Dermoscopy of a skin lesion:
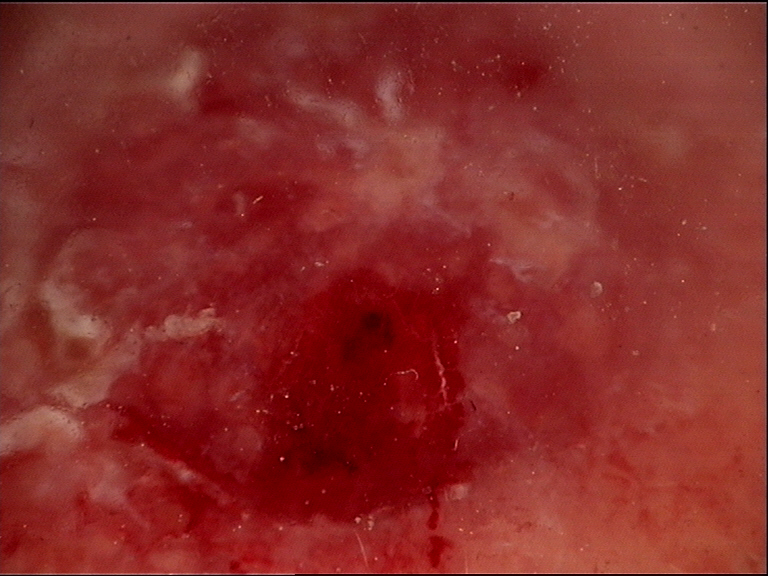Q: What did the workup show?
A: squamous cell carcinoma (biopsy-proven)